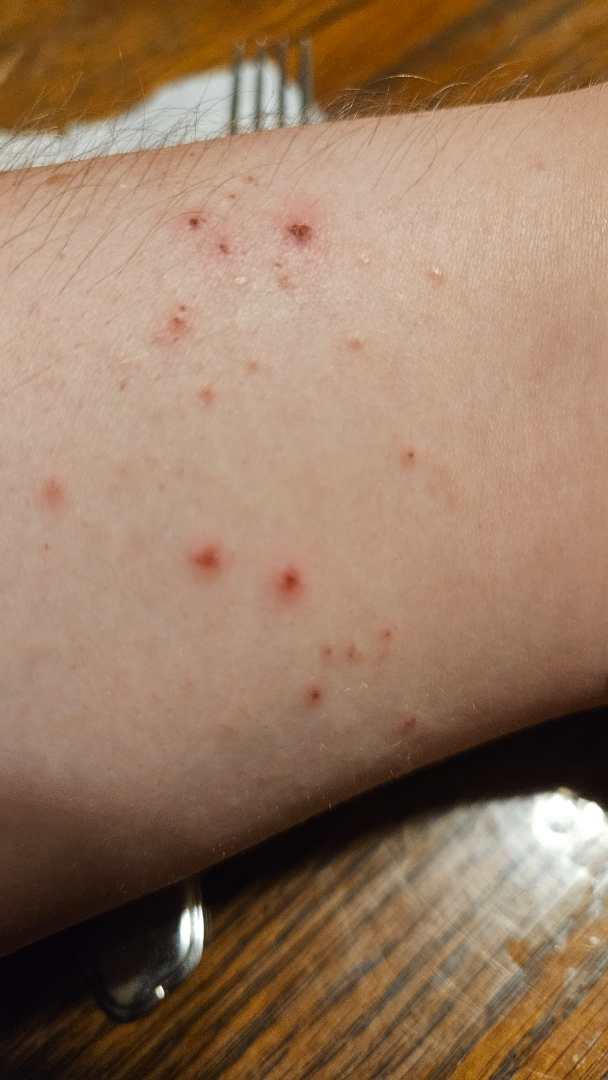patient: male, age 30–39
patient describes the issue as: a rash
reported symptoms: none reported
view: close-up
systemic symptoms: none reported
history: one to four weeks
texture: flat
anatomic site: arm
assessment: the impression is Eczema